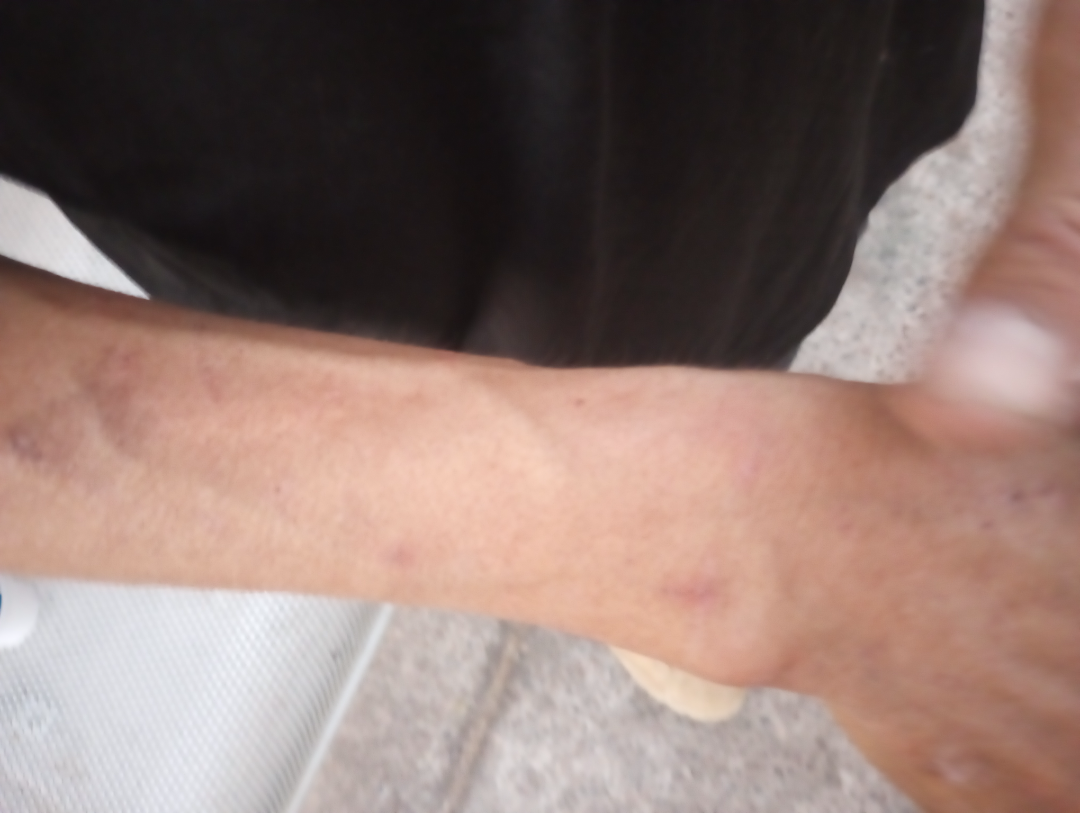- assessment — could not be assessed
- framing — close-up